The patient is FST II; a male patient aged 73 to 77.
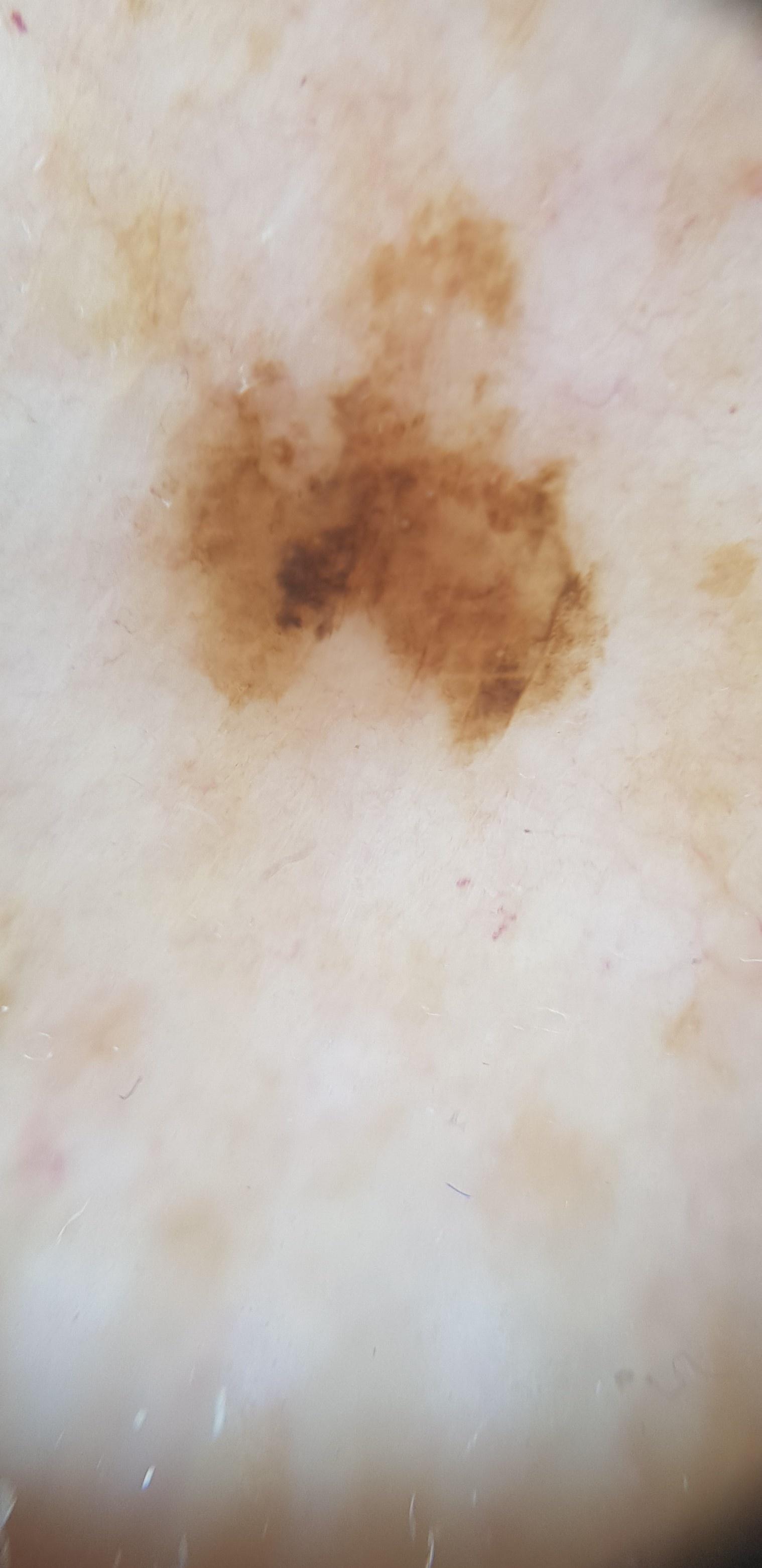  diagnosis:
    name: Nevus
    malignancy: benign
    confirmation: histopathology
    lineage: melanocytic